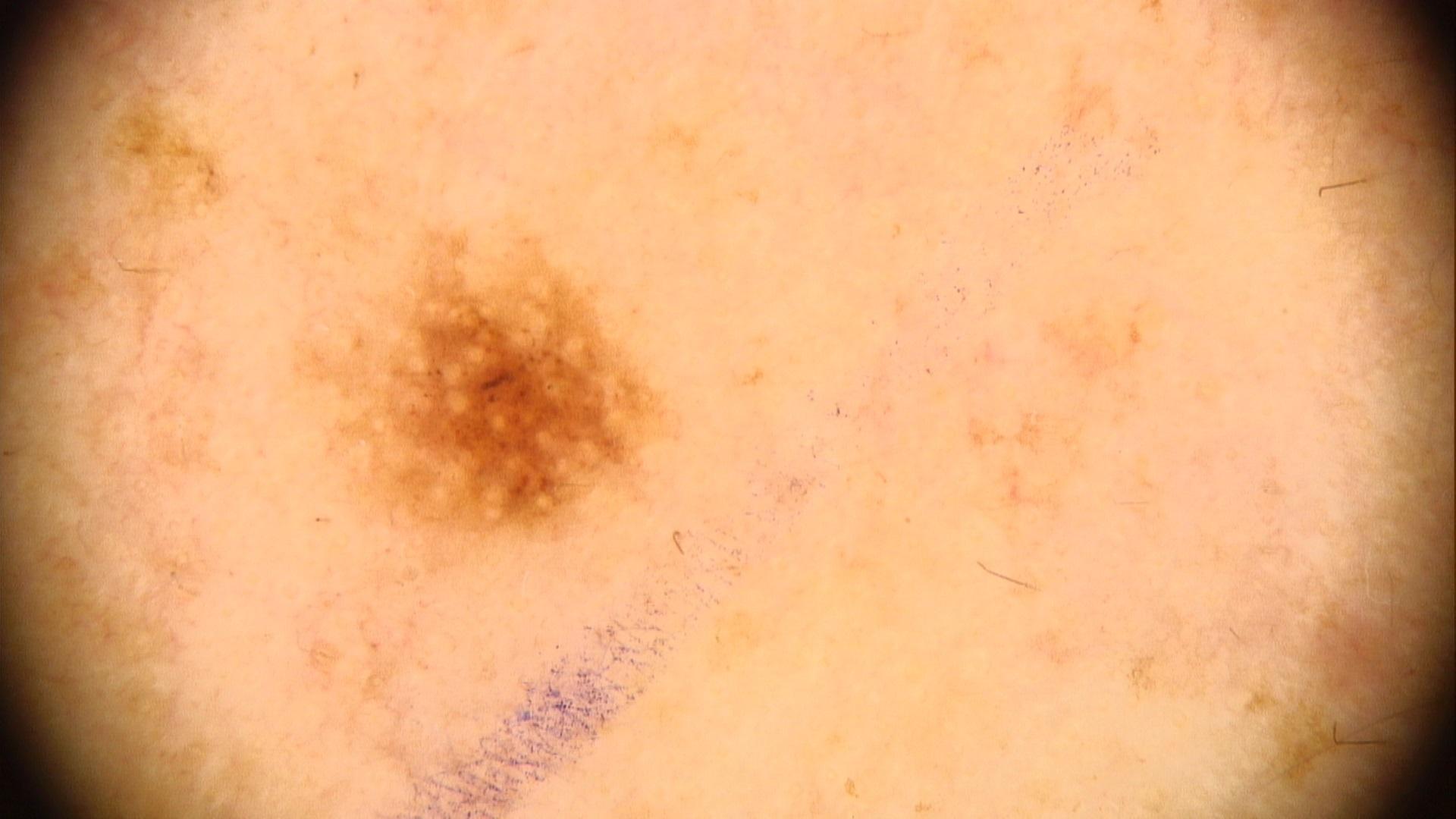{"diagnosis": {"name": "Nevus", "malignancy": "benign", "confirmation": "expert clinical impression", "lineage": "melanocytic"}}